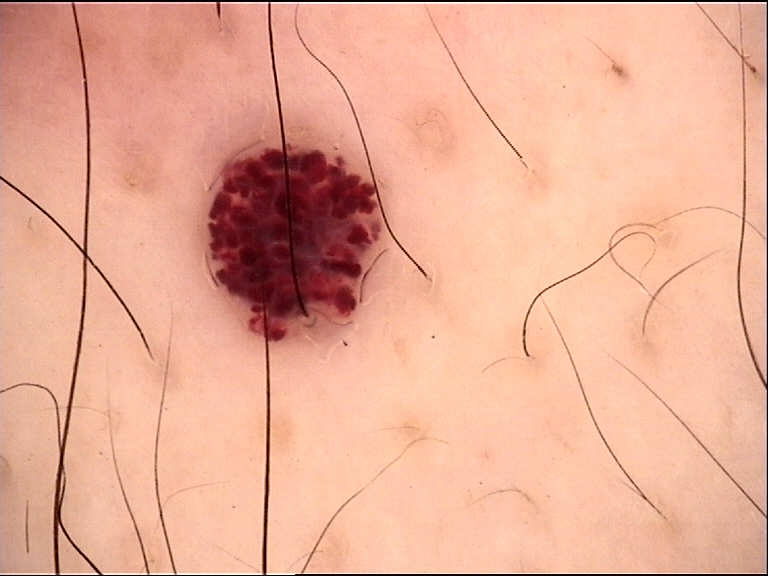image type — dermatoscopy | subtype — junctional, dysplastic | label — Spitz/Reed nevus (expert consensus).